A dermatoscopic image of a skin lesion.
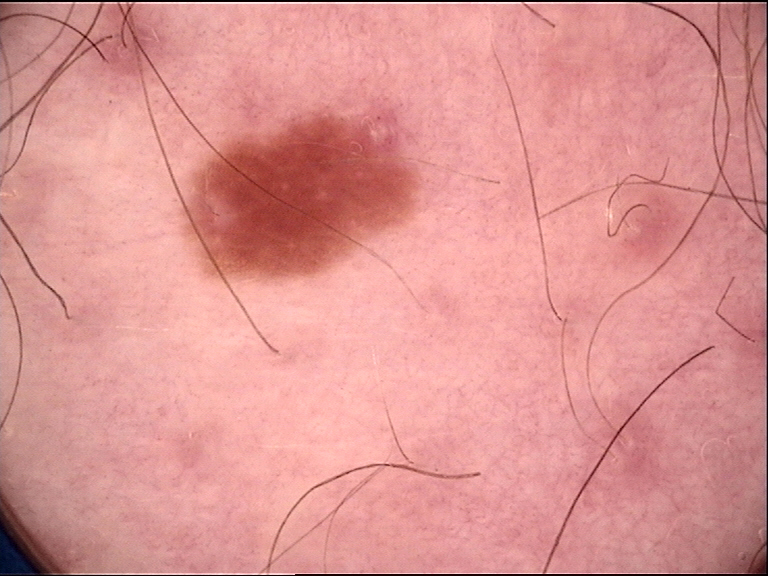Conclusion: Consistent with a dysplastic junctional nevus.